This image was taken at a distance · the lesion involves the back of the torso and front of the torso:
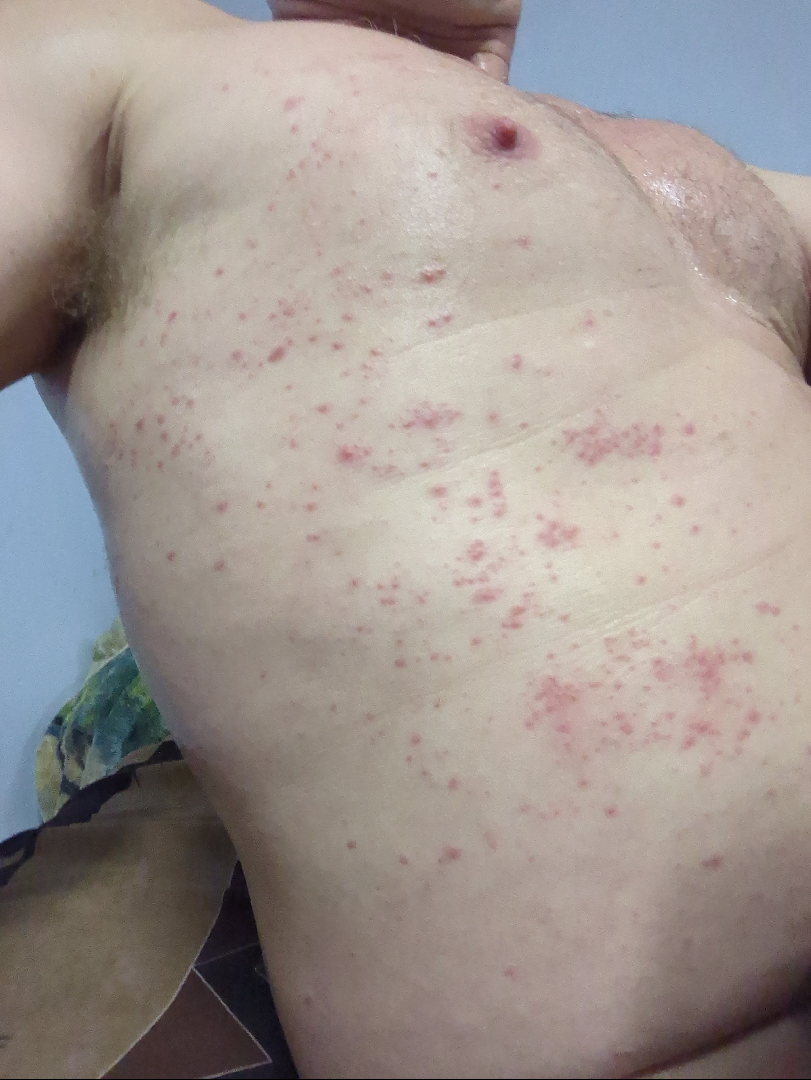Q: What was the assessment?
A: unable to determine